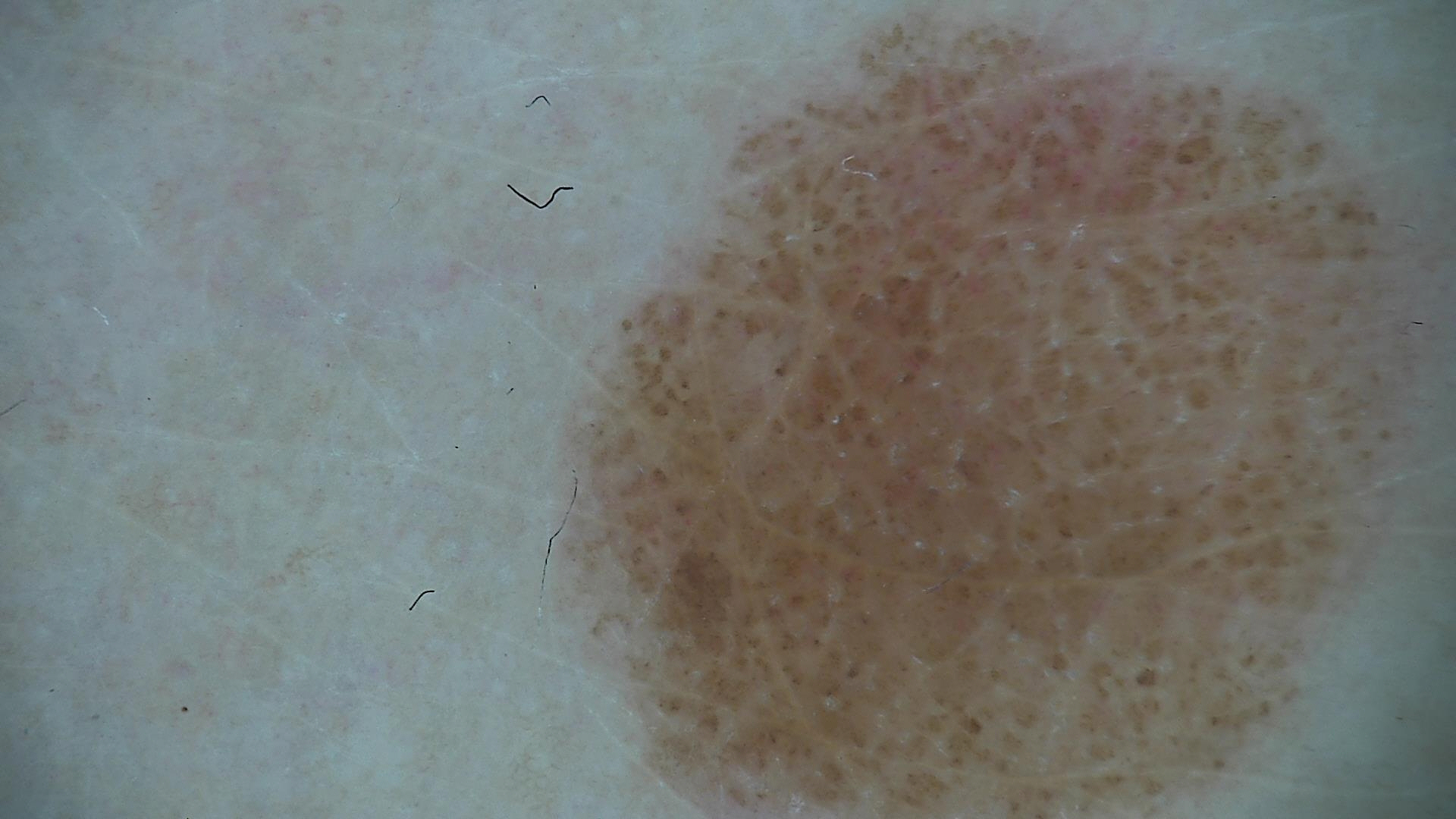Q: What is the diagnosis?
A: compound nevus (expert consensus)